The affected area is the arm; close-up view.
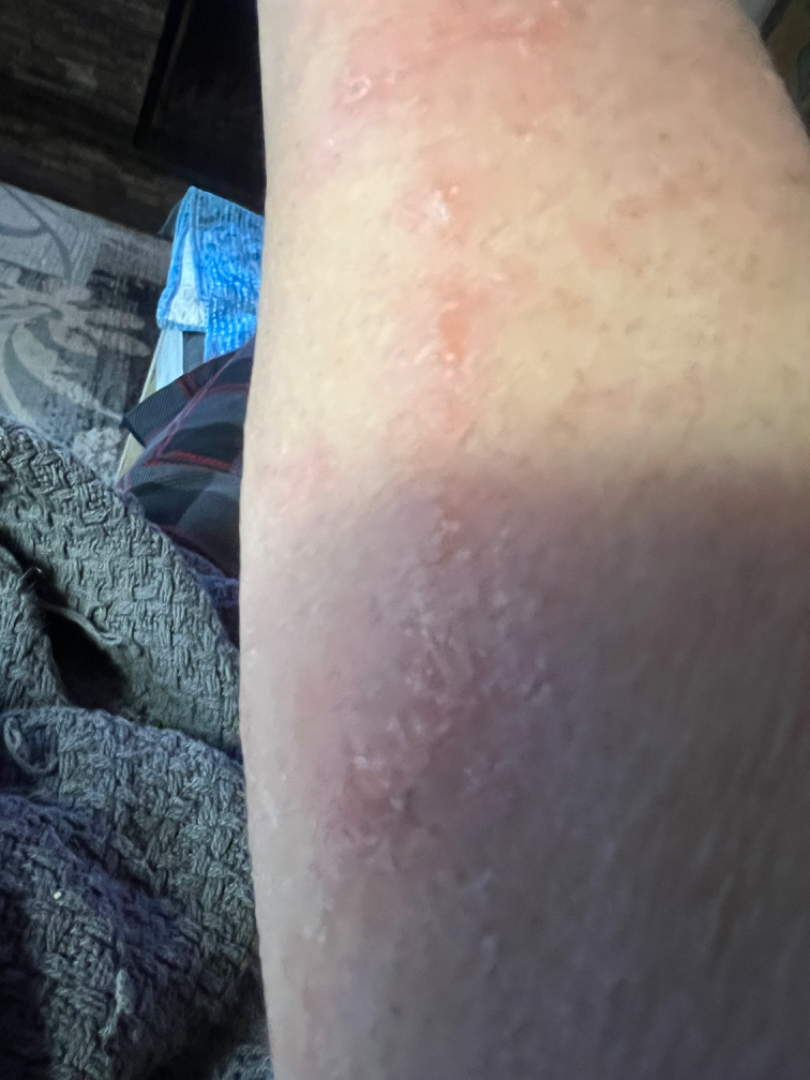{
  "assessment": "unable to determine"
}